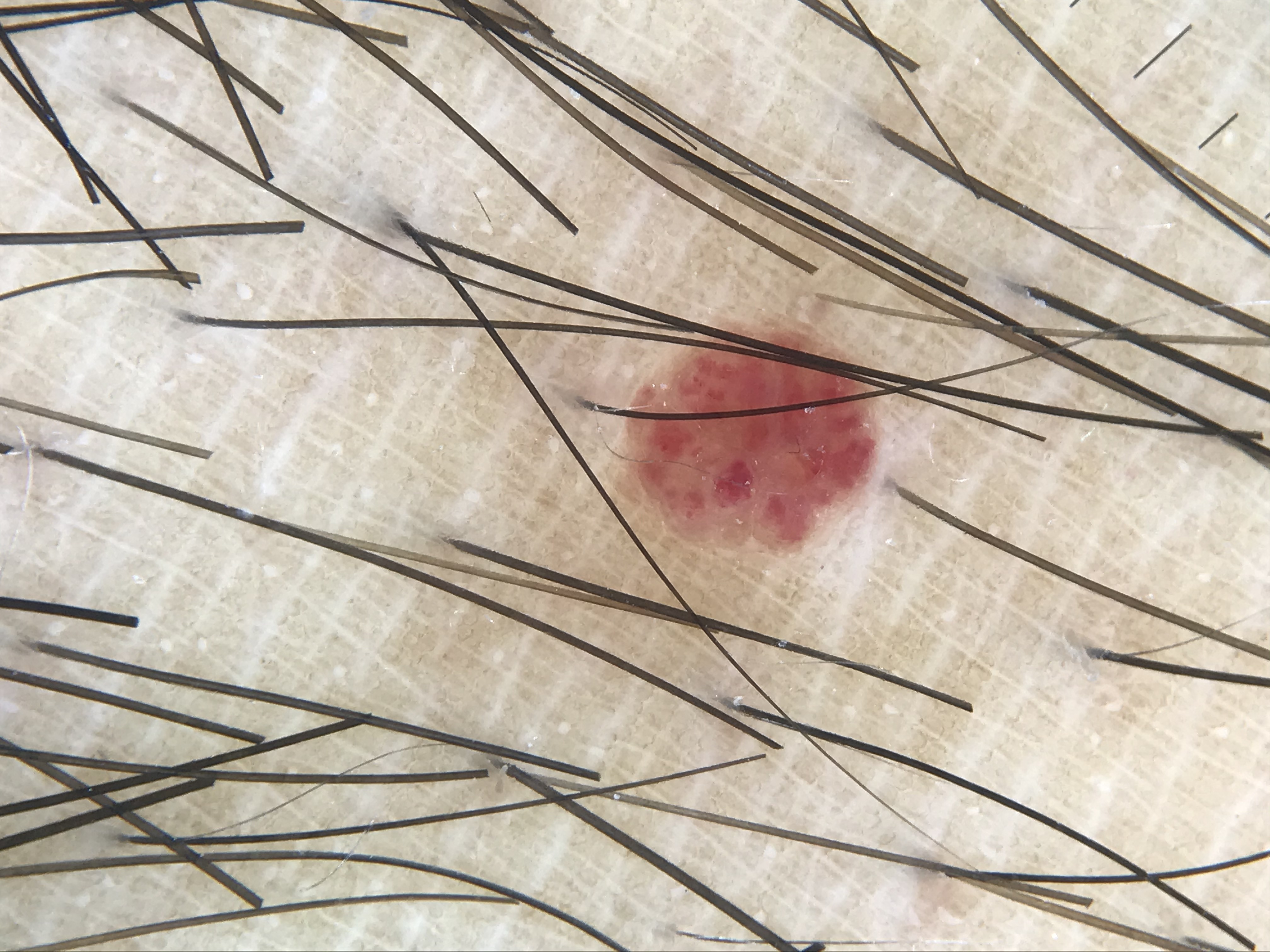Classified as a benign lesion — a hemangioma.